This is a dermoscopic photograph of a skin lesion. A female patient aged 13-17 — 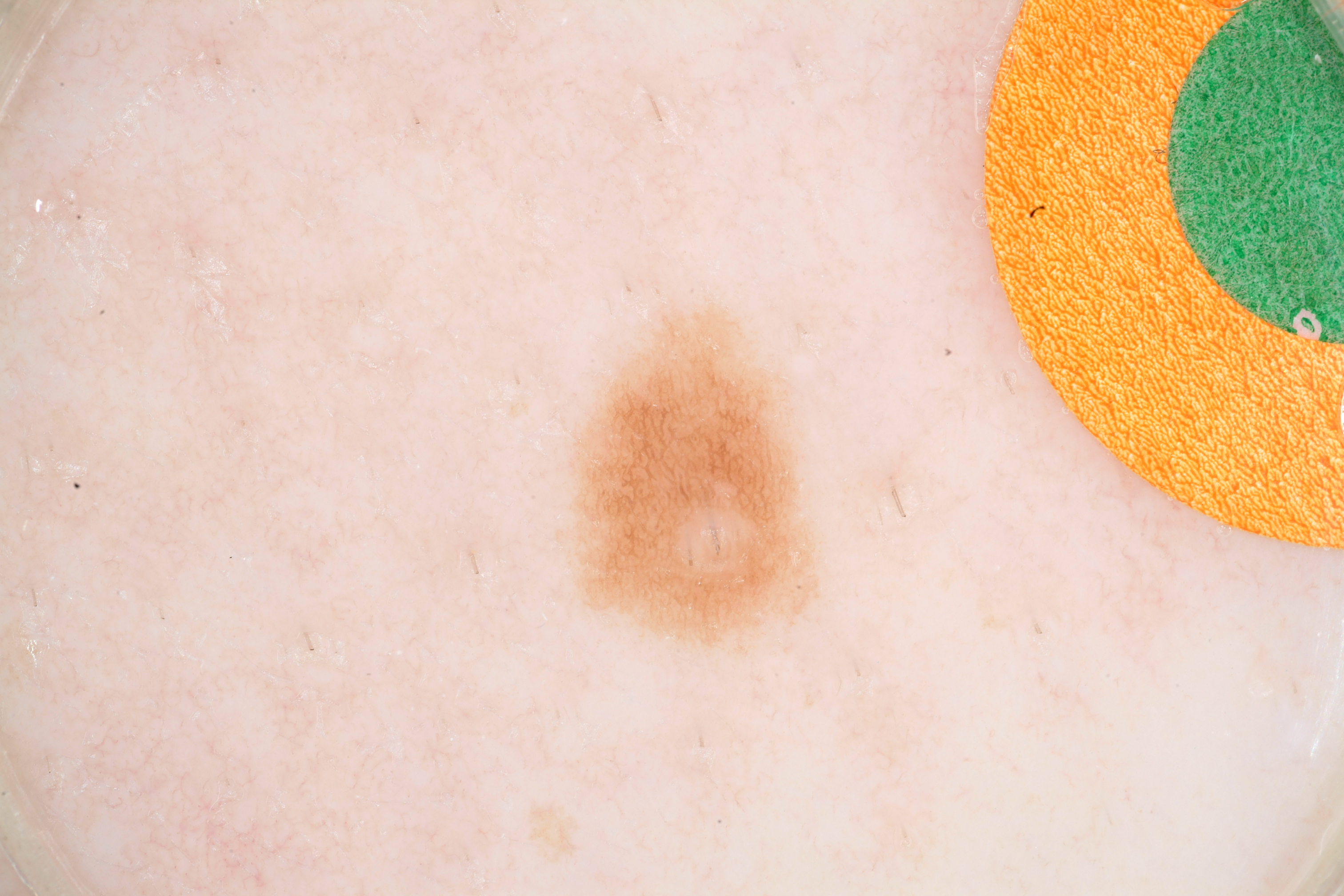lesion bbox: x1=555 y1=299 x2=822 y2=657 | lesion size: small | dermoscopic features: pigment network | assessment: a melanocytic nevus.